The lesion involves the head or neck. The patient described the issue as a rash. Texture is reported as raised or bumpy and rough or flaky. The patient indicates itching. This is a close-up image. Present for one to four weeks:
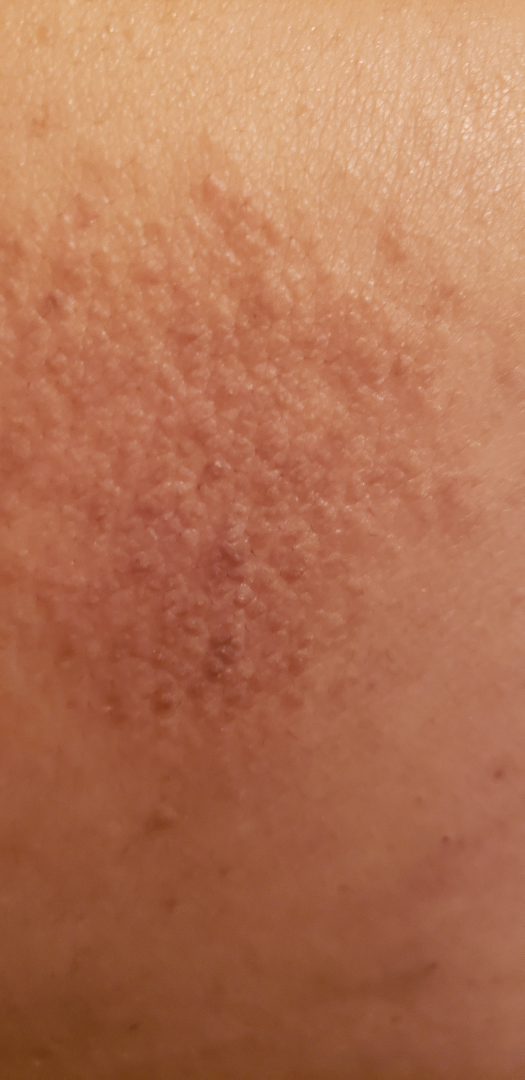assessment: could not be assessed.